The patient was assessed as Fitzpatrick III; the chart documents a previous melanoma; a contact-polarized dermoscopy image of a skin lesion; a female patient aged 68-72.
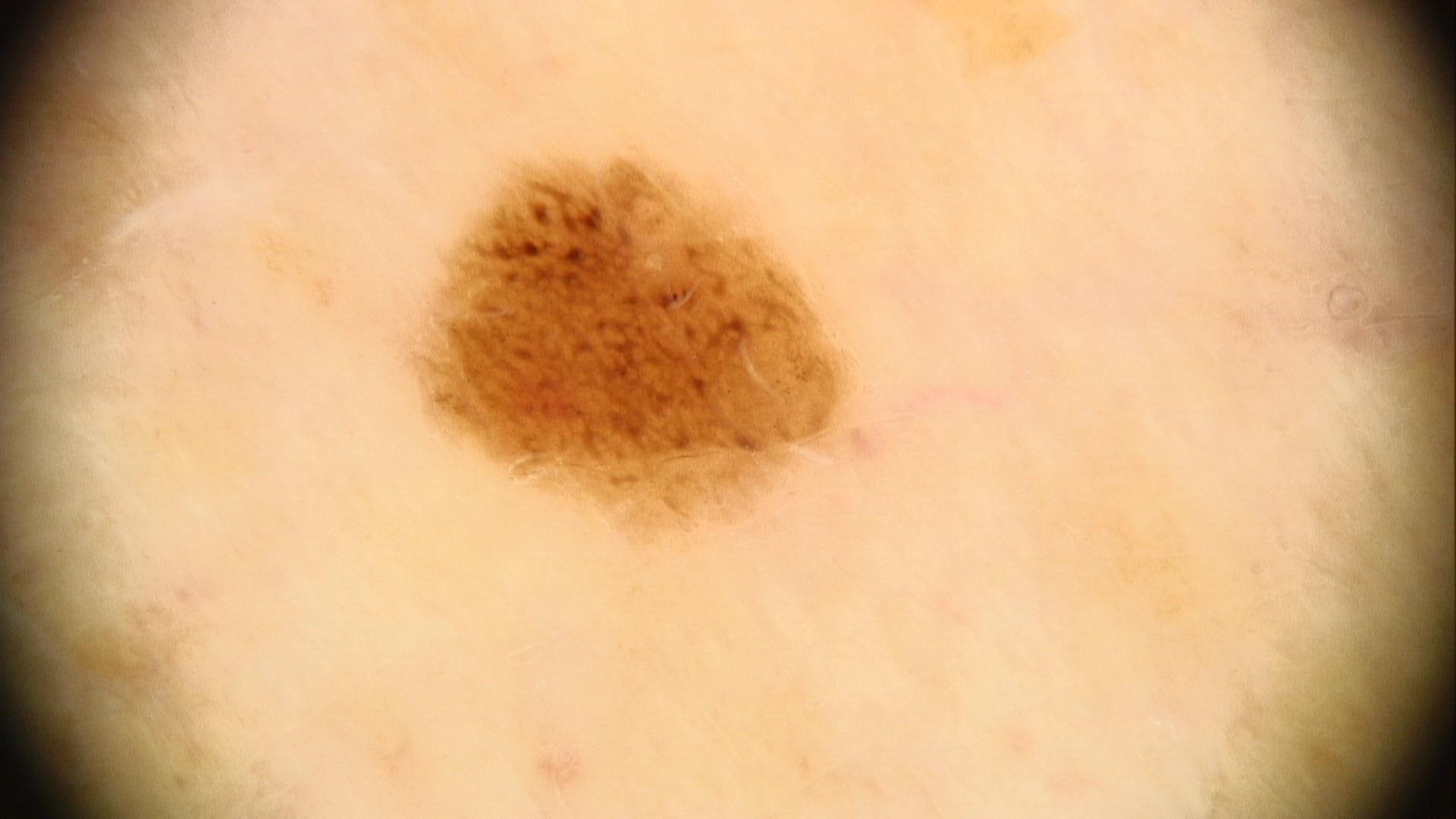The lesion is located on a lower extremity. Histopathology confirmed a skin cancer — a melanoma.